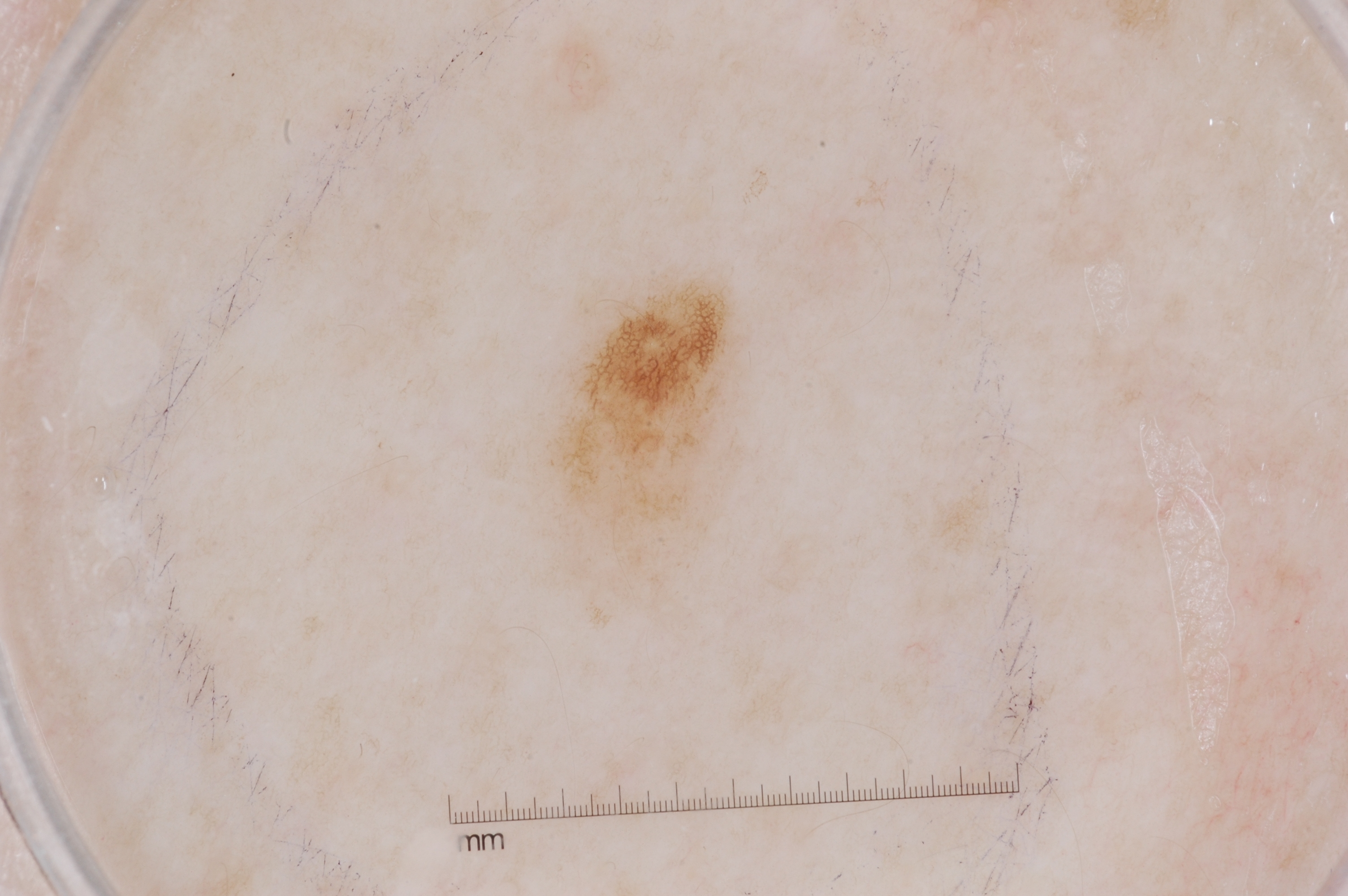Case summary:
The patient is a female aged 53 to 57. A dermoscopy image of a single skin lesion. Dermoscopic review identifies pigment network. With coordinates (x1, y1, x2, y2), the lesion is located at box(537, 265, 750, 627). The lesion covers approximately 4% of the dermoscopic field.
Conclusion:
The diagnostic assessment was a melanocytic nevus.